A dermoscopic close-up of a skin lesion:
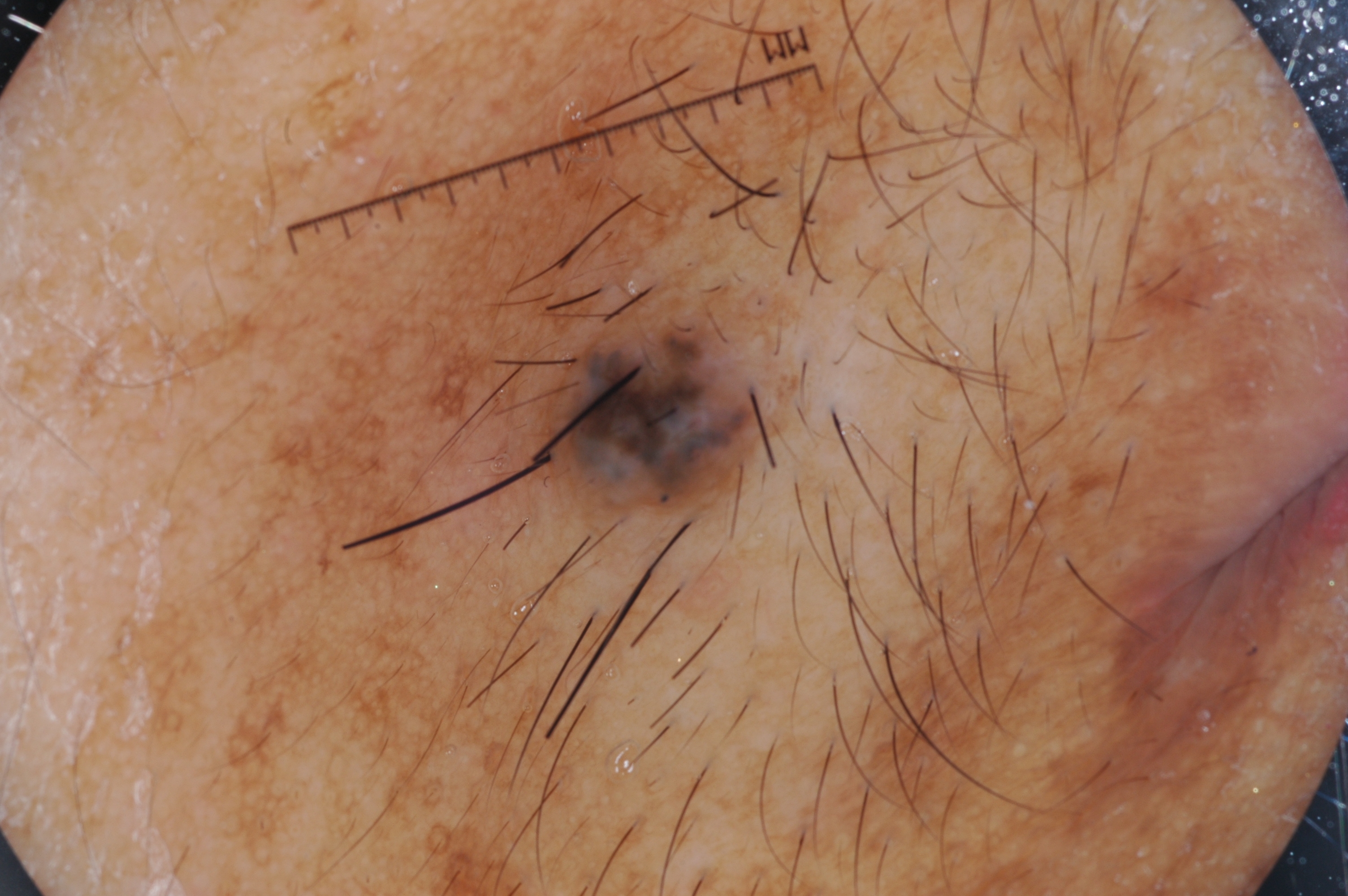| key | value |
|---|---|
| dermoscopic features not present | milia-like cysts, negative network, streaks, and pigment network |
| bounding box | <bbox>549, 258, 833, 526</bbox> |
| extent | small |
| impression | a melanocytic nevus, a benign lesion |